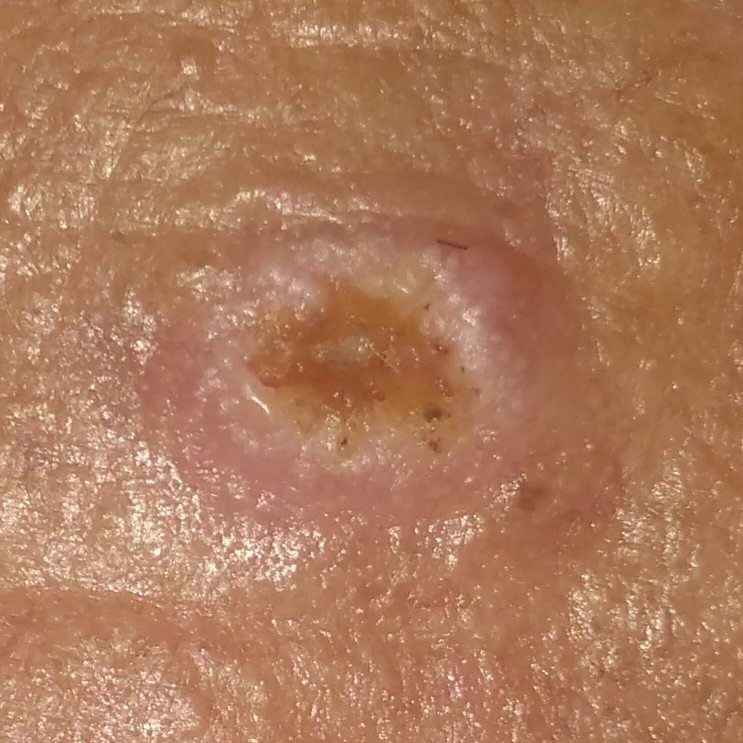subject = male, 70 years of age; image = smartphone clinical photo; risk factors = prior malignancy (patient or family), alcohol use, no pesticide exposure, no tobacco use; FST = II; anatomic site = the face; size = 11 × 9 mm; symptoms = elevation, itching, growth / no bleeding, no pain; diagnosis = squamous cell carcinoma (biopsy-proven).